Located on the leg and arm · no relevant systemic symptoms · the contributor is 30–39, female · the patient indicates the condition has been present for less than one week · the photograph was taken at a distance.
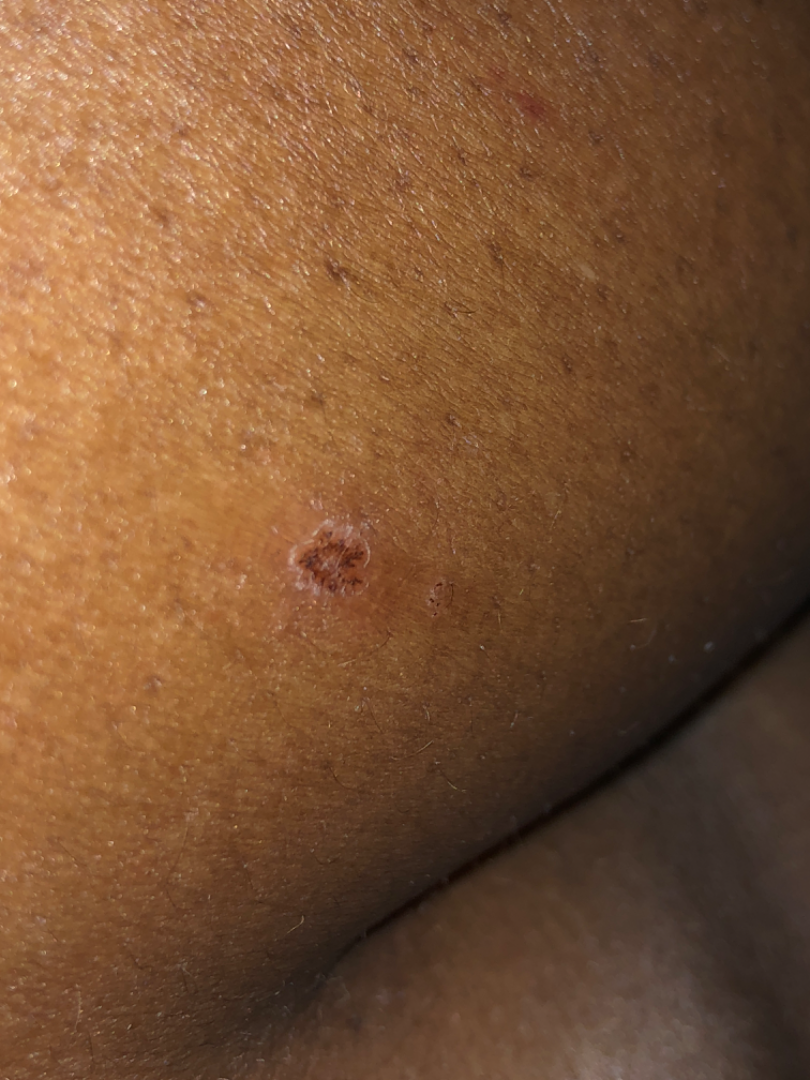Assessment:
Diagnostic features were not clearly distinguishable in this photograph.